The lesion is associated with itching and burning. Texture is reported as raised or bumpy. No associated systemic symptoms reported. Reported duration is about one day. This is a close-up image. The contributor is a male aged 60–69. Located on the back of the torso, arm, front of the torso and back of the hand. The patient described the issue as a rash.
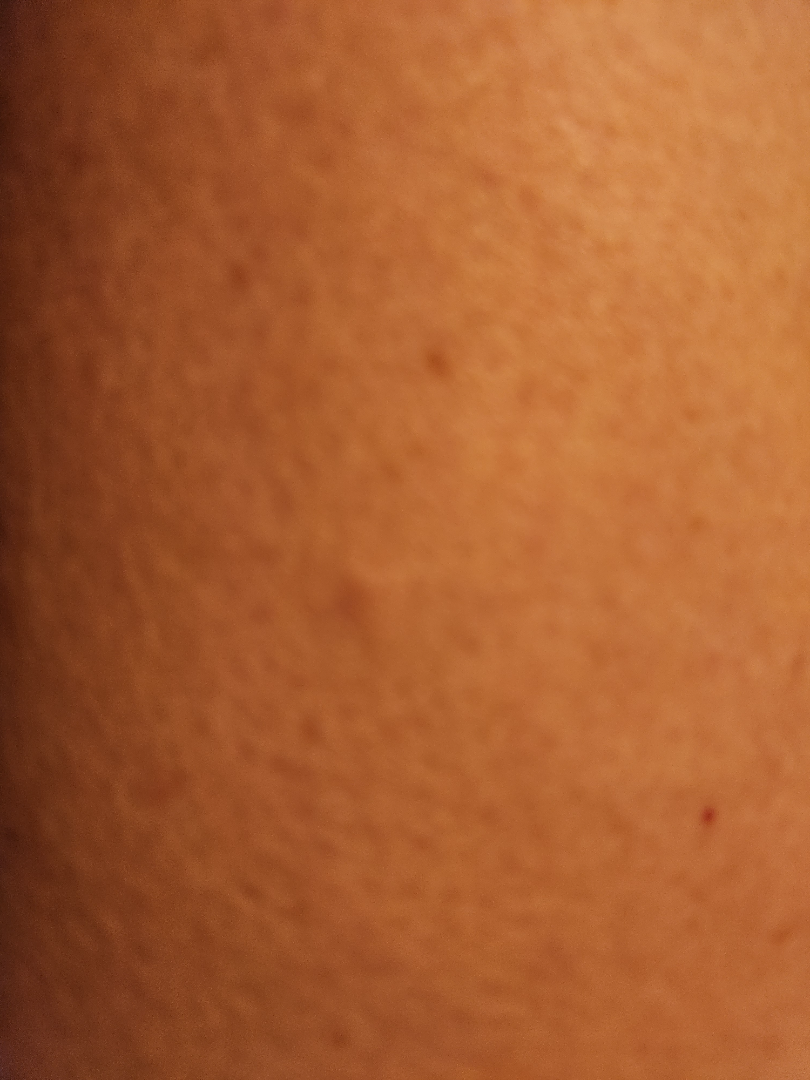Case summary:
– differential diagnosis — the leading consideration is Dermatofibroma